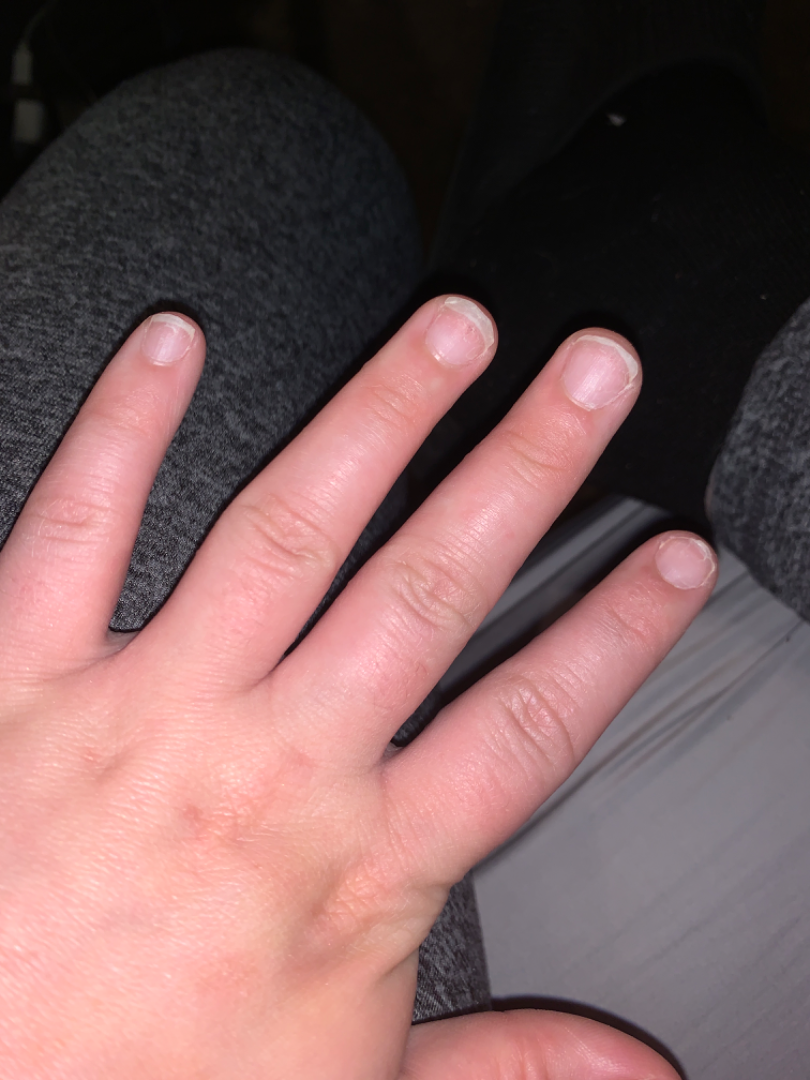On teledermatology review: Eczema (favored); Scabies (lower probability); Hypersensitivity (lower probability).